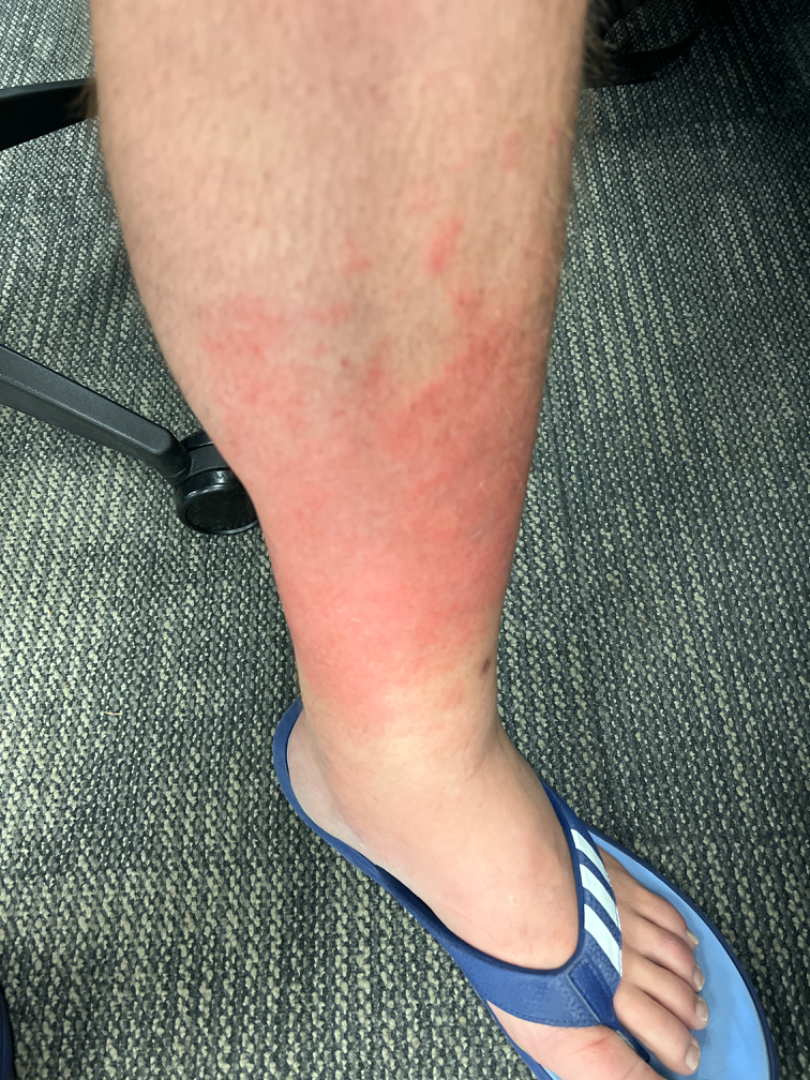The condition could not be reliably identified from the image.
The photograph was taken at a distance.
The patient is a male aged 30–39.
Present for less than one week.
The leg is involved.
Self-categorized by the patient as a rash.
Texture is reported as flat and rough or flaky.
Symptoms reported: pain, bothersome appearance, burning and enlargement.
Self-reported Fitzpatrick skin type III.